Close-up view. The lesion involves the leg:
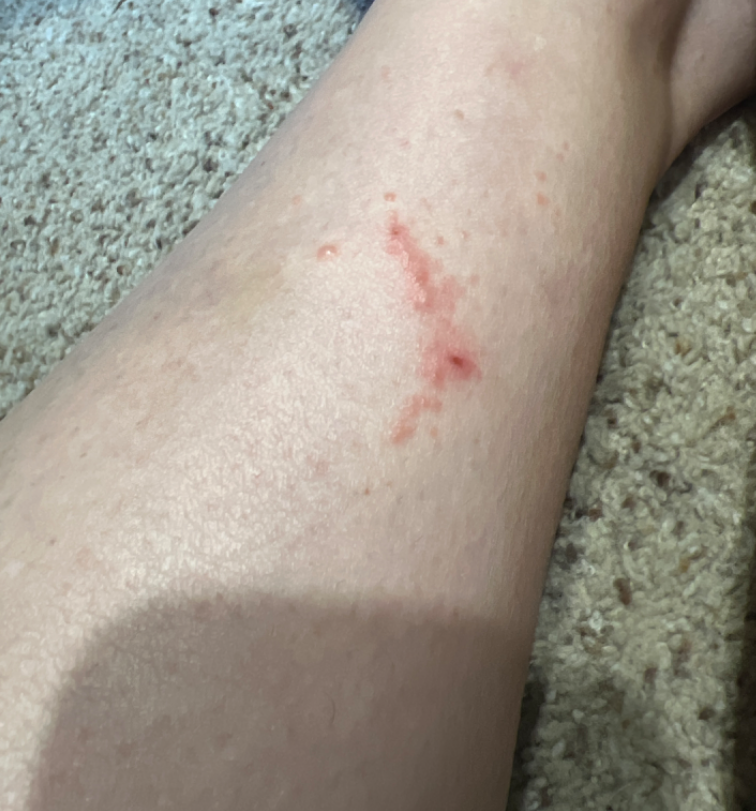{"symptoms": ["pain", "bothersome appearance", "itching"], "patient_category": "a rash", "differential": {"tied_lead": ["Cutaneous larva migrans", "Allergic Contact Dermatitis"], "unlikely": ["Localized skin infection"]}}